The photograph is a close-up of the affected area; the arm and leg are involved.
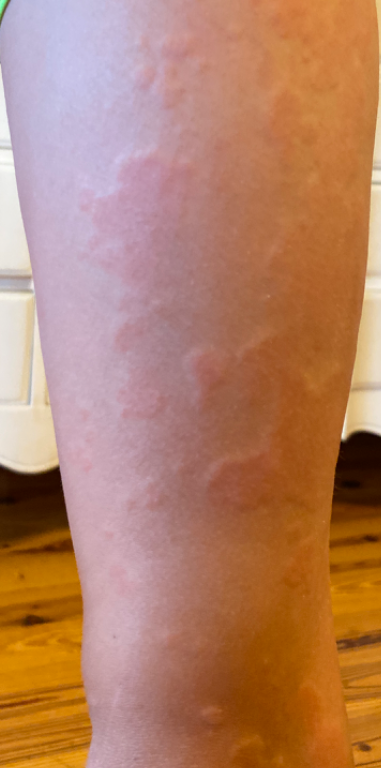Review:
Urticaria (weight 0.55); Annular erythema (weight 0.27); Drug Rash (weight 0.18).